A dermoscopic image of a skin lesion, the patient is a female about 60 years old: 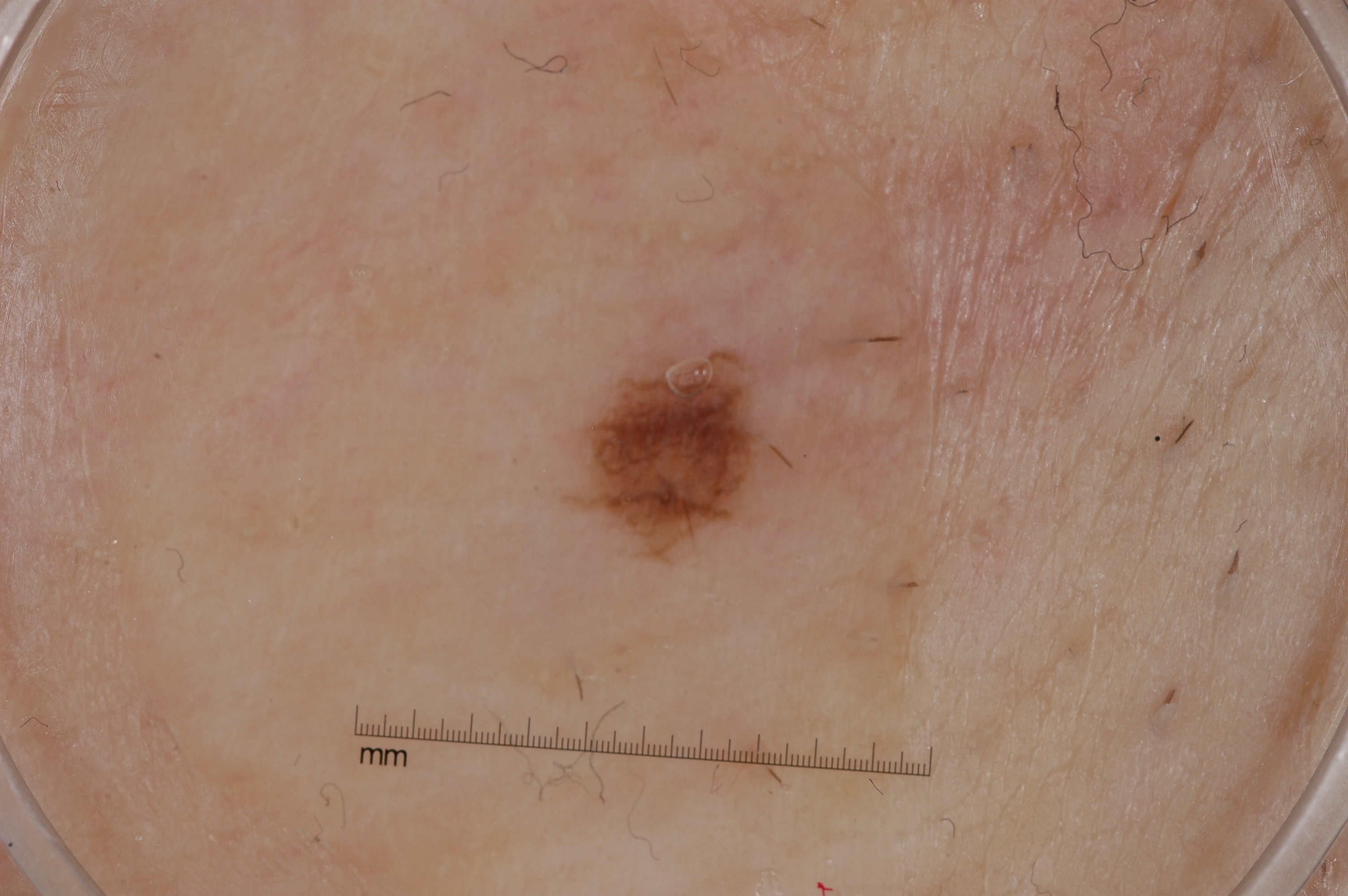Notes:
- dermoscopic pattern: pigment network
- lesion location: 585, 349, 794, 561
- diagnosis: a melanocytic nevus, a benign skin lesion